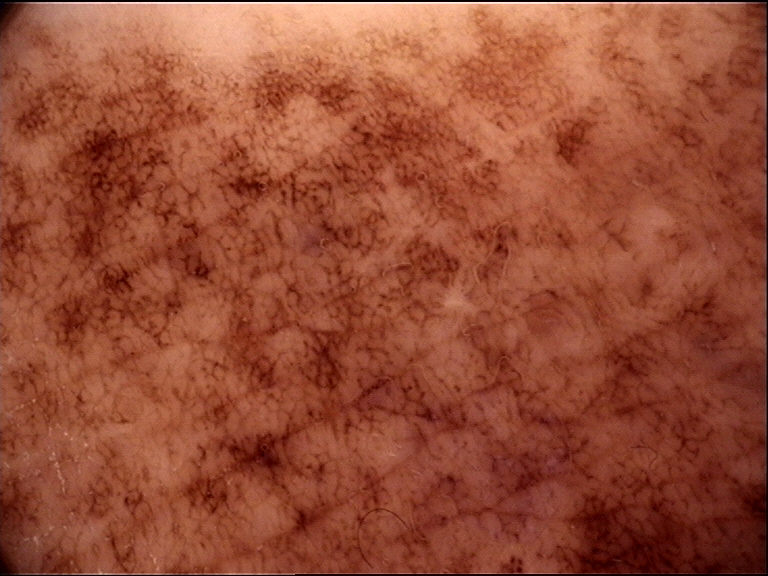class: congenital junctional nevus (expert consensus).